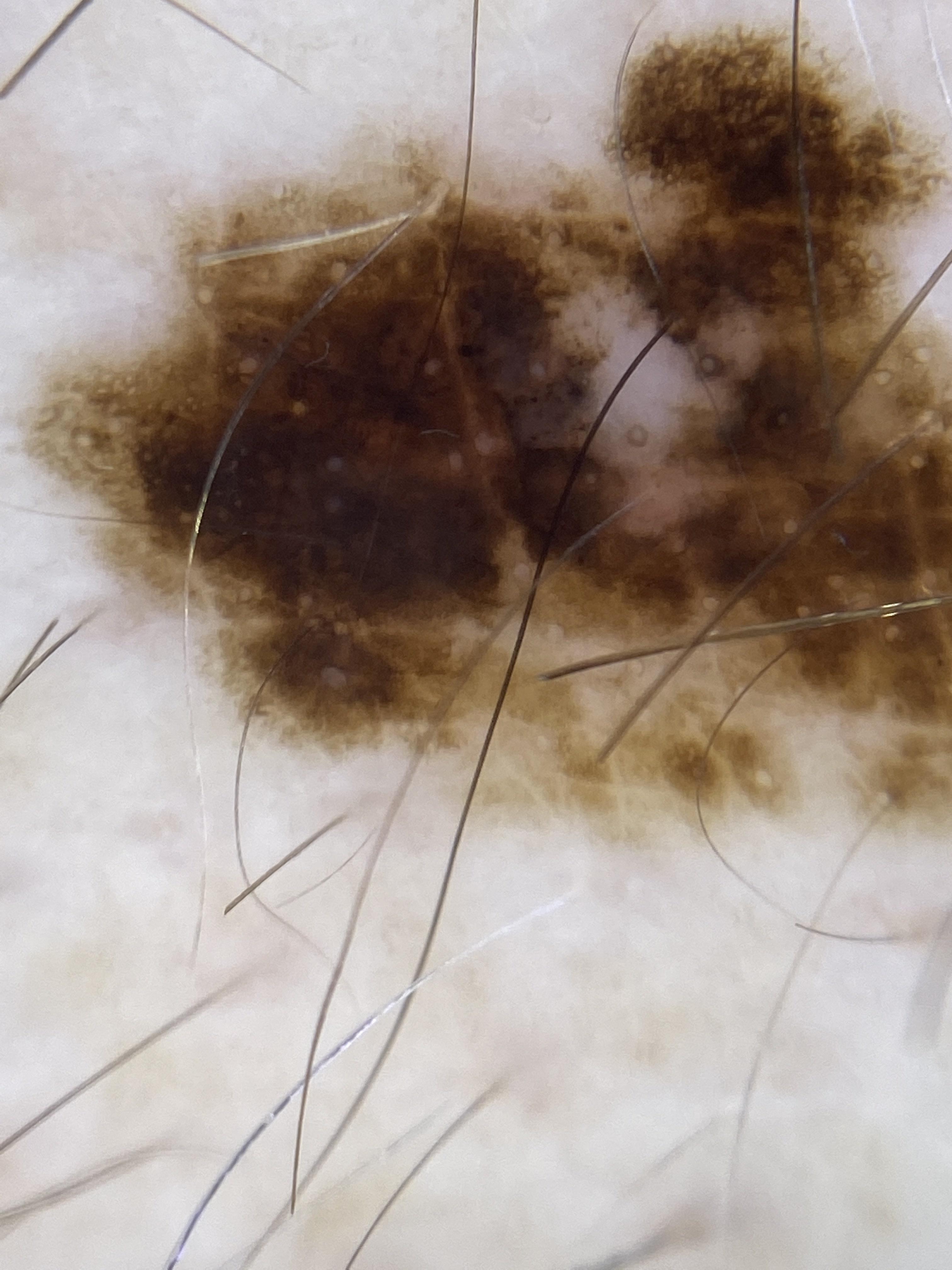A male patient about 70 years old. Histopathology confirmed a melanoma.